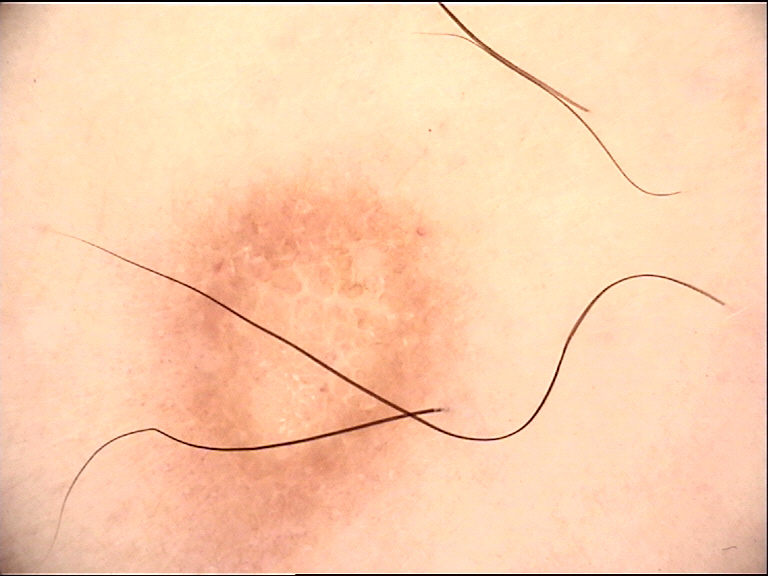{
  "image": "dermatoscopy",
  "lesion_type": {
    "main_class": "fibro-histiocytic"
  },
  "diagnosis": {
    "name": "dermatofibroma",
    "code": "df",
    "malignancy": "benign",
    "super_class": "non-melanocytic",
    "confirmation": "expert consensus"
  }
}